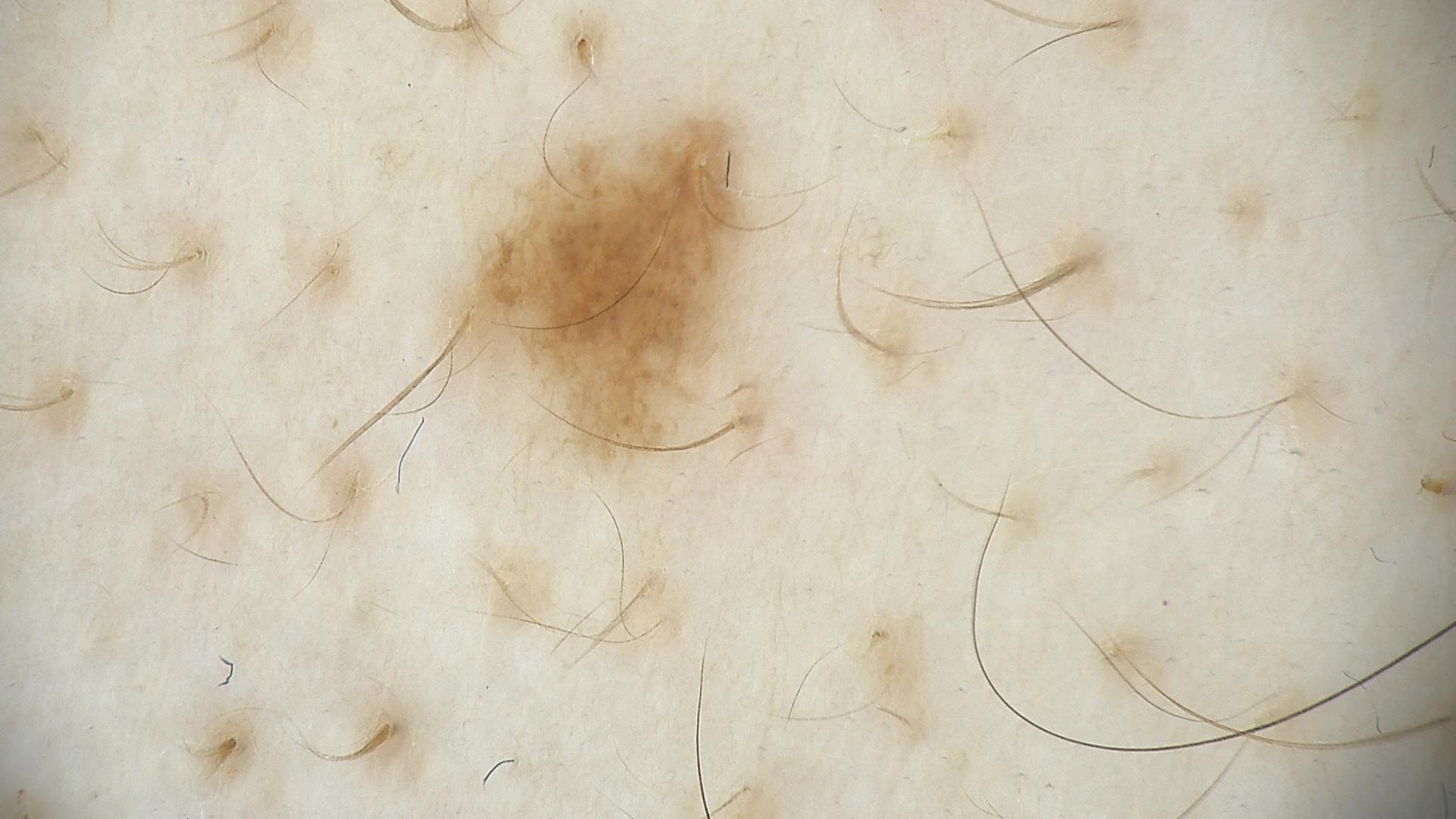Findings:
A dermoscopic photograph of a skin lesion.
Impression:
Labeled as a dysplastic junctional nevus.